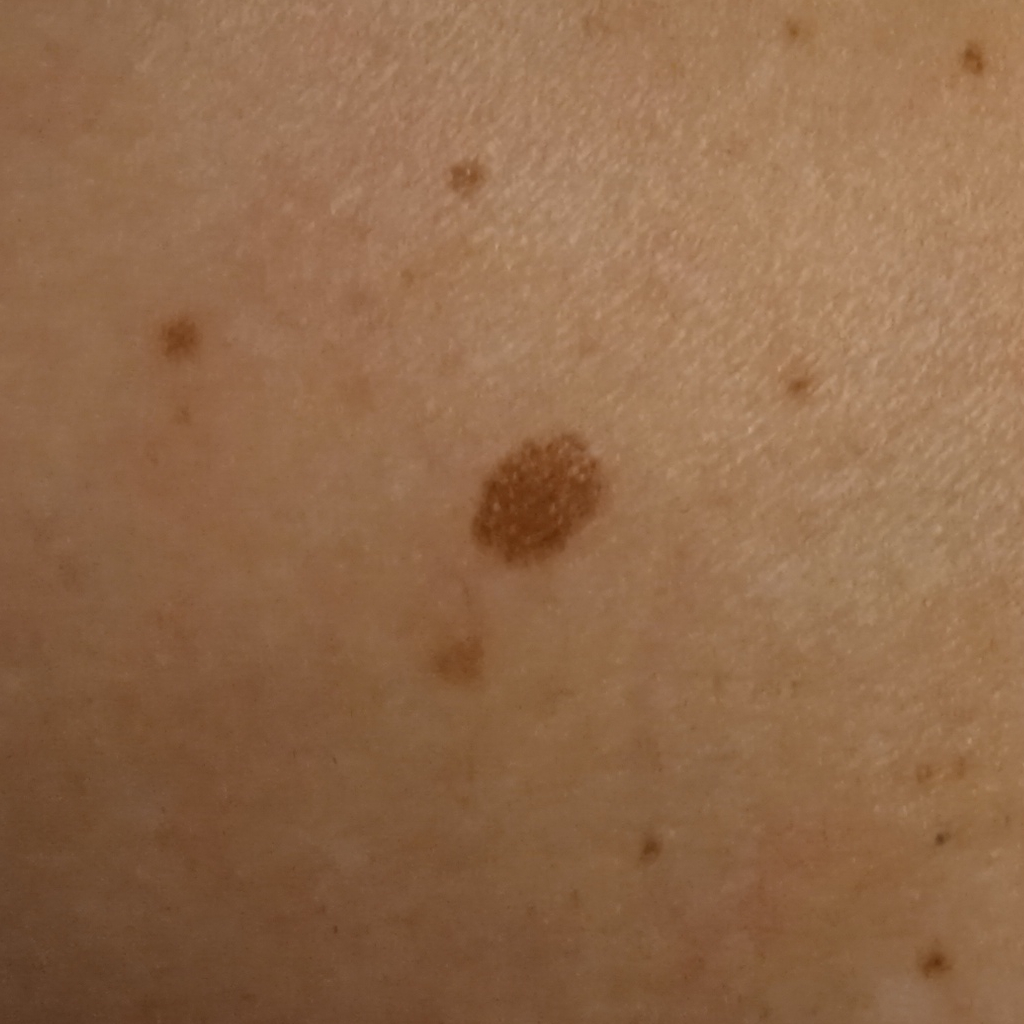Q: What is the referral context?
A: clinical suspicion of melanocytic nevus
Q: What is the patient's nevus burden?
A: a moderate number of melanocytic nevi
Q: What kind of image is this?
A: clinical photograph
Q: Tell me about the patient.
A: female, aged 59
Q: What is the anatomic site?
A: an arm
Q: Lesion size?
A: 6.7 mm
Q: What did the biopsy show?
A: atypical (dysplastic) nevus — biopsy-proven